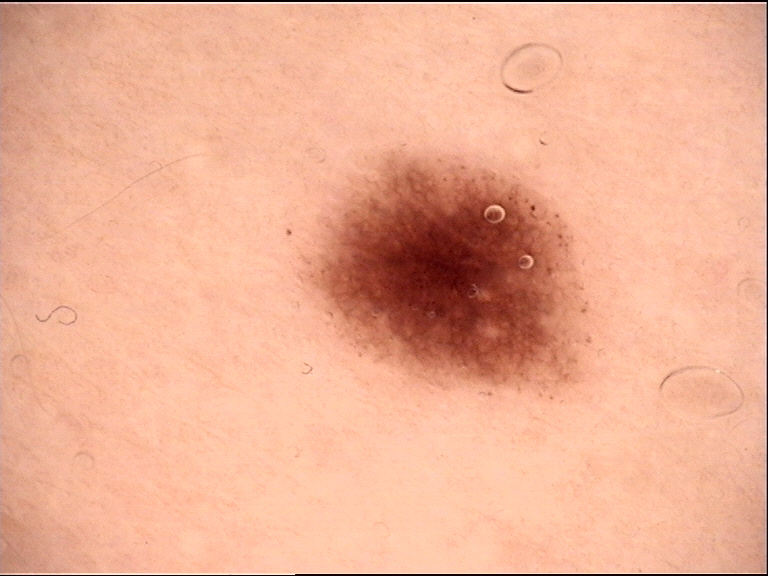Q: What was the diagnostic impression?
A: dysplastic junctional nevus (expert consensus)